Female patient, age 60–69 · the arm is involved · a close-up photograph:
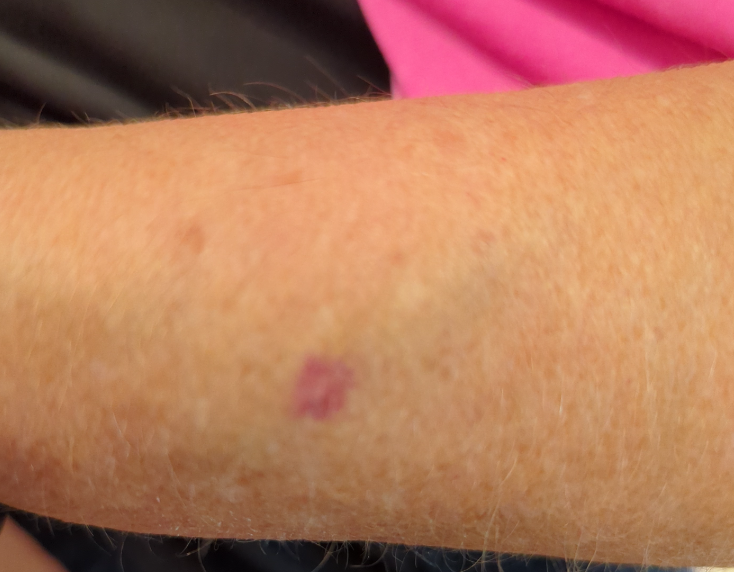Q: Could the case be diagnosed?
A: unable to determine
Q: How does the lesion feel?
A: flat
Q: When did this start?
A: less than one week